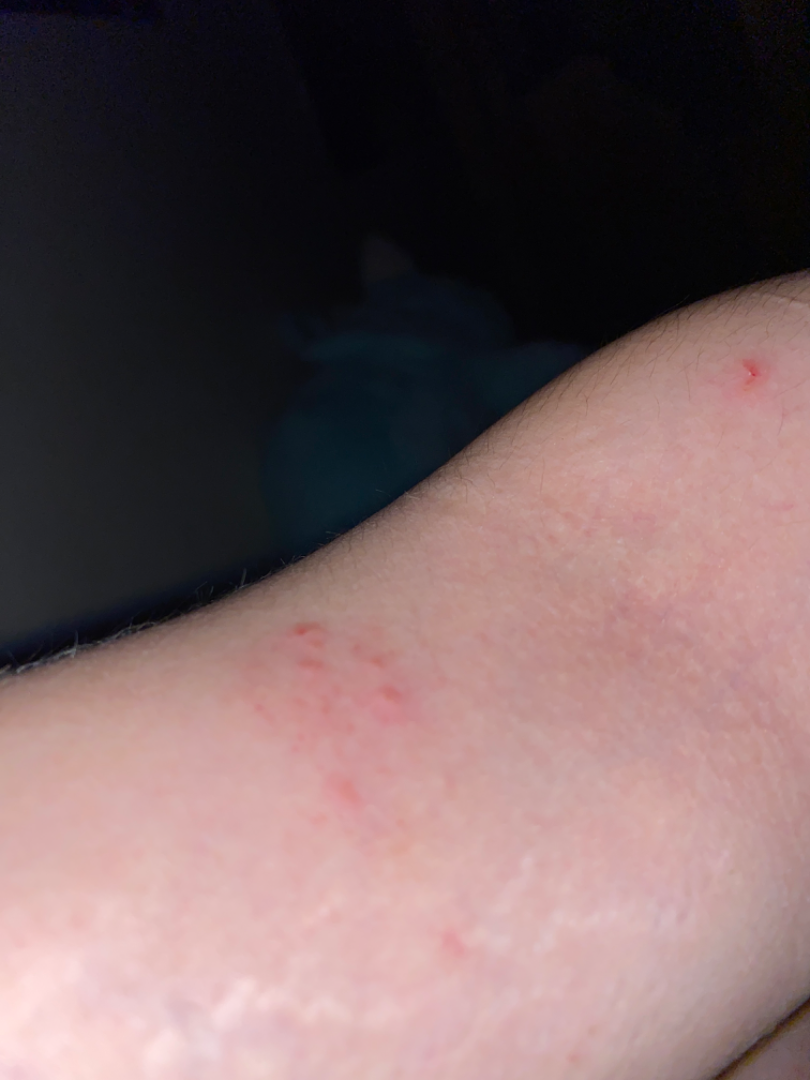The contributor reports the lesion is raised or bumpy and fluid-filled. Reported duration is less than one week. Located on the arm. The patient is 18–29, female. Skin tone: Fitzpatrick III; human graders estimated Monk Skin Tone 2. The contributor reports enlargement and itching. No relevant systemic symptoms. This image was taken at an angle. Three independent reviewers: Allergic Contact Dermatitis; Acute dermatitis, NOS; and Irritant Contact Dermatitis were each considered, in no particular order; less probable is Insect Bite; a remote consideration is Eczema.